A male subject 77 years of age; acquired for a research image collection, with no referral diagnosis; a clinical photograph of a skin lesion — 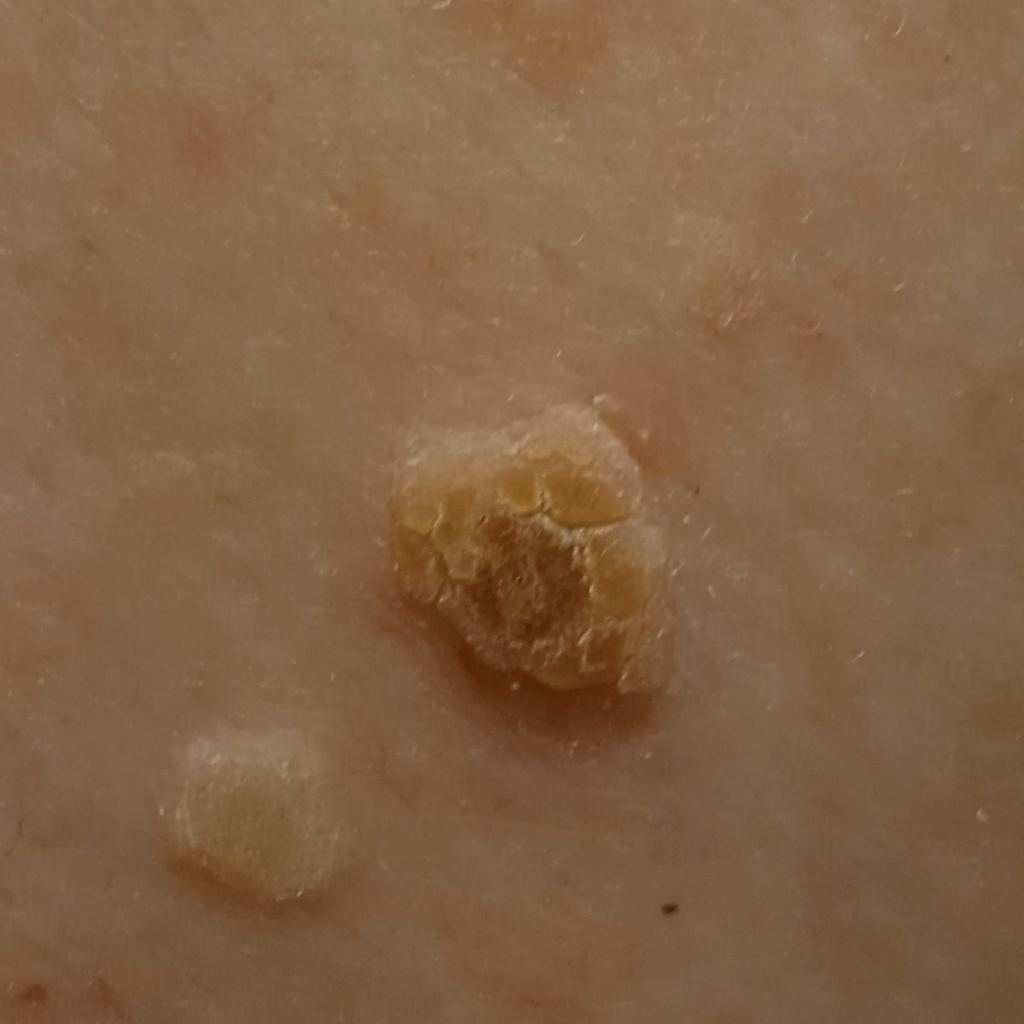Summary:
The lesion is on the back. The lesion is about 11.1 mm across.
Conclusion:
The consensus diagnosis for this lesion was an actinic keratosis.